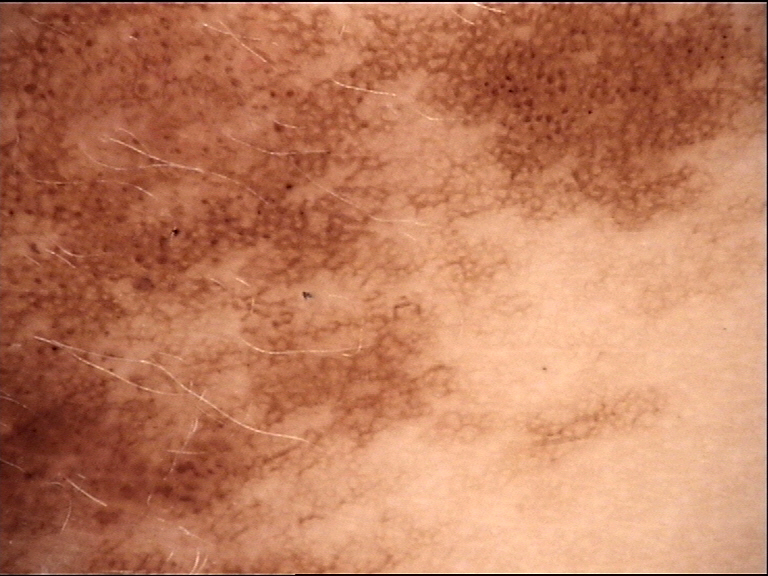lesion type = banal
diagnosis = congenital junctional nevus (expert consensus)